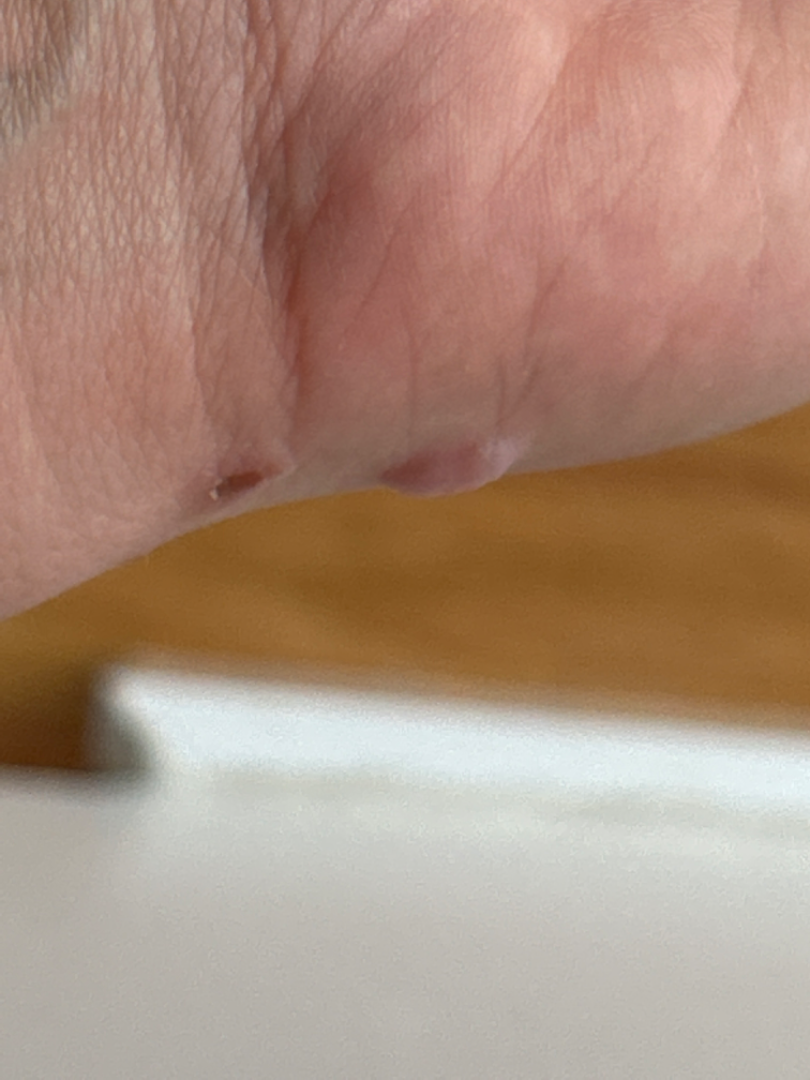On photographic review by a dermatologist, Lichen planus/lichenoid eruption and Molluscum Contagiosum were considered with similar weight.